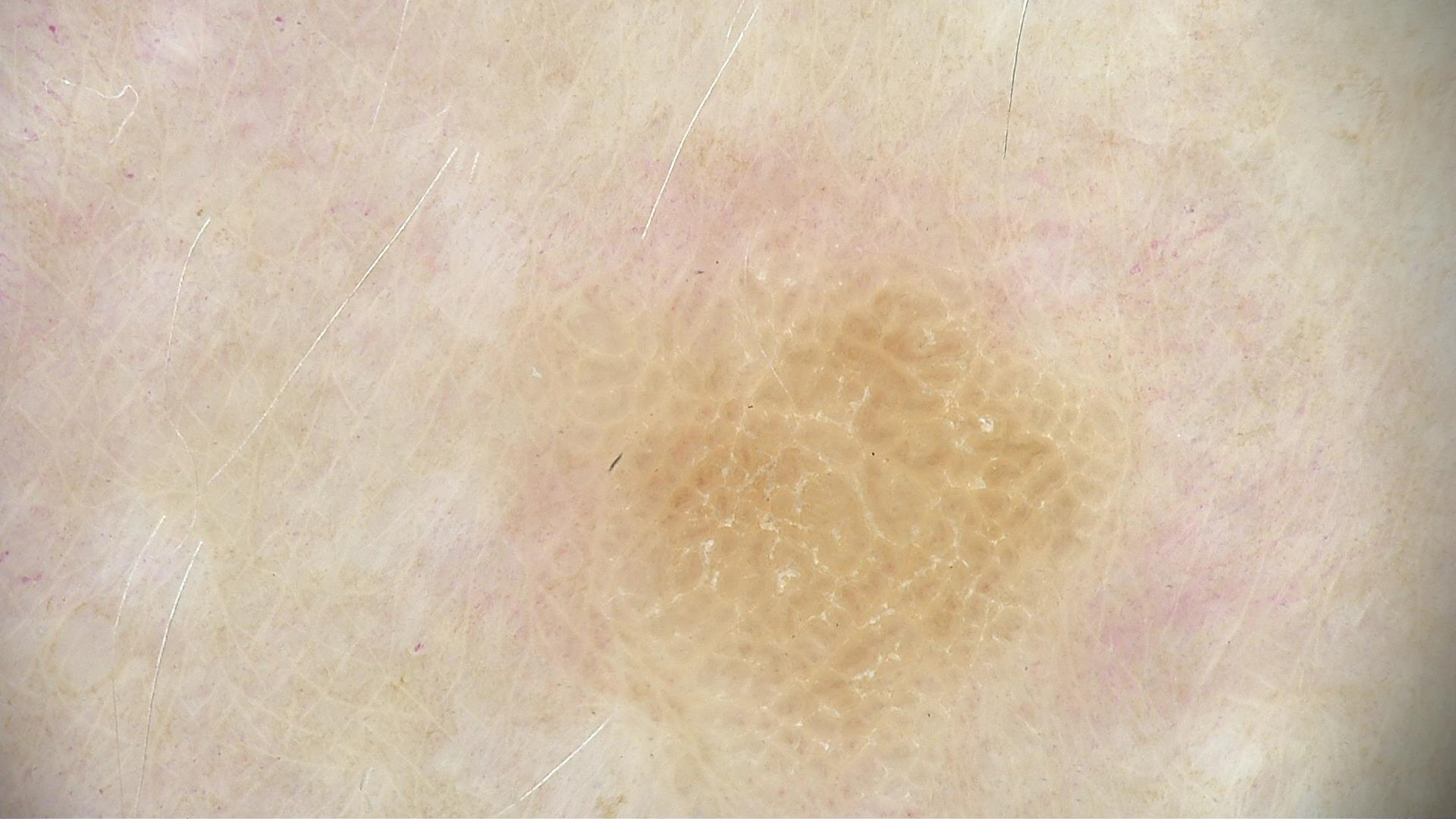classification = keratinocytic
label = seborrheic keratosis (expert consensus)